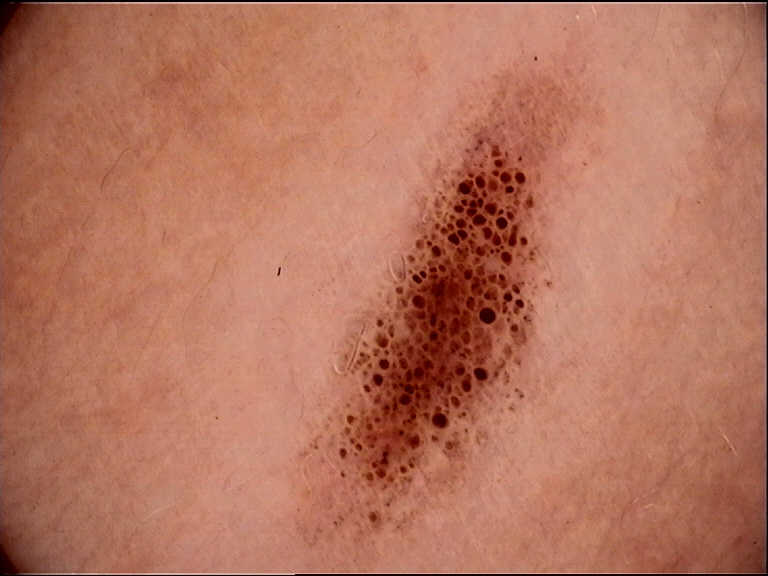image type = dermatoscopy | class = dysplastic compound nevus (expert consensus).